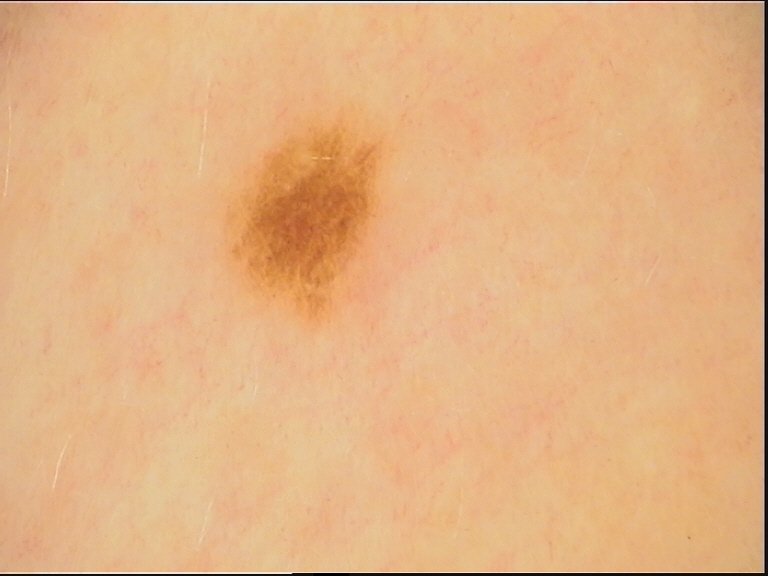The diagnosis was a dysplastic junctional nevus.